A clinical photograph showing a skin lesion · the chart notes no prior malignancy (patient or family) · a female subject 72 years of age.
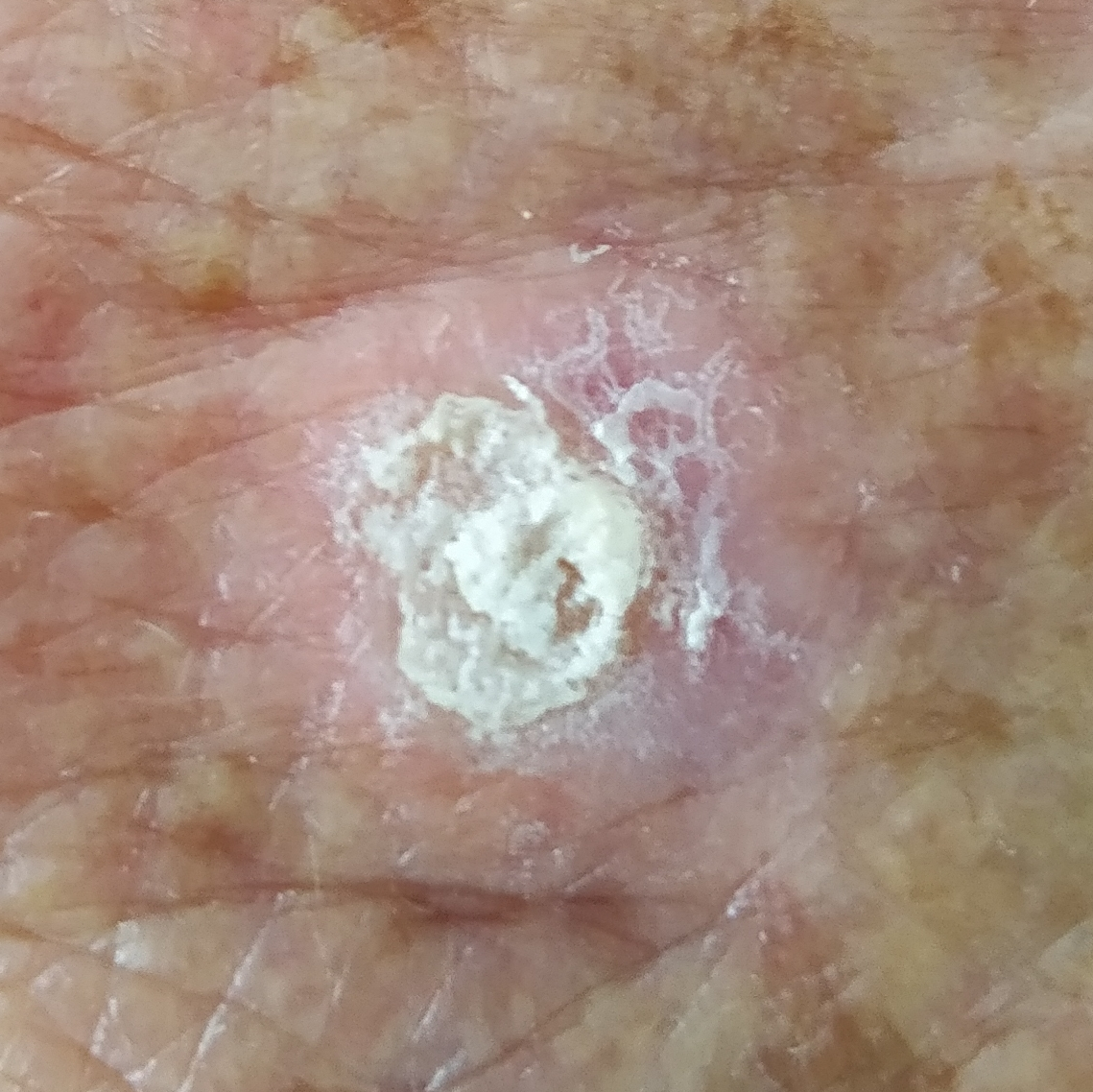The patient describes that the lesion is elevated, itches, has grown, and has changed.
Histopathological examination showed a lesion of indeterminate malignant potential — an actinic keratosis.